The photograph is a close-up of the affected area.
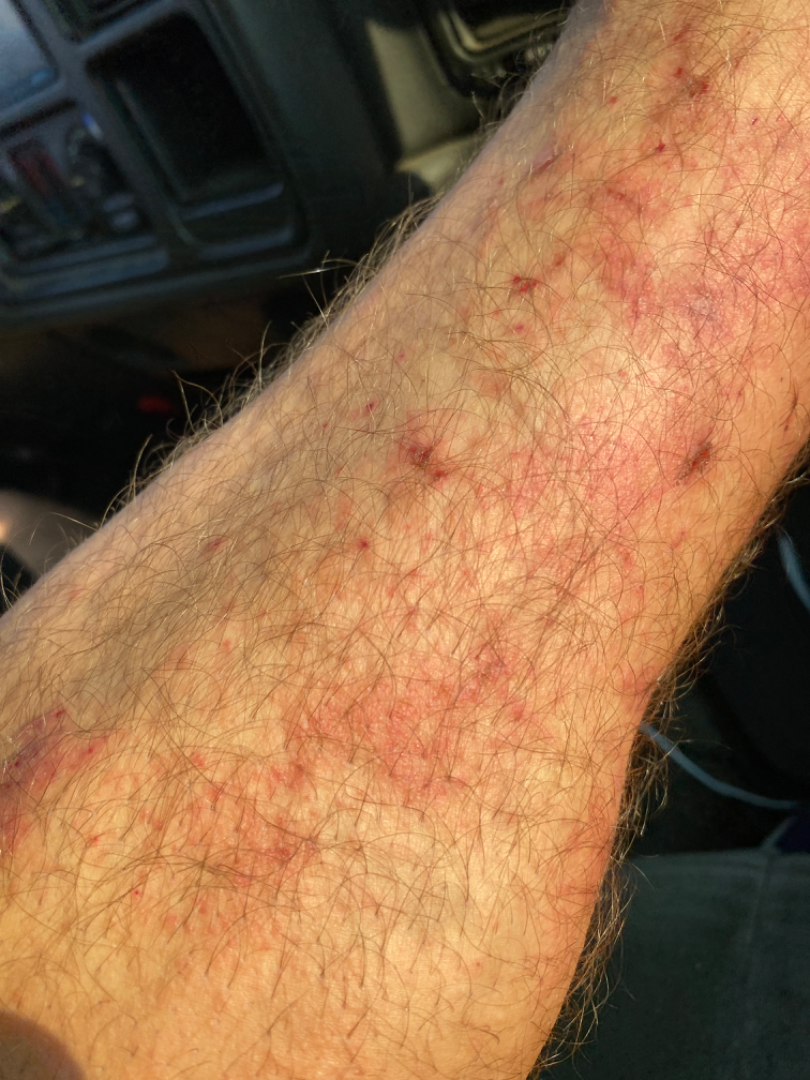| field | value |
|---|---|
| assessment | unable to determine |